Reported duration is less than one week; Fitzpatrick phototype III; located on the leg; an image taken at an angle; self-categorized by the patient as a rash: 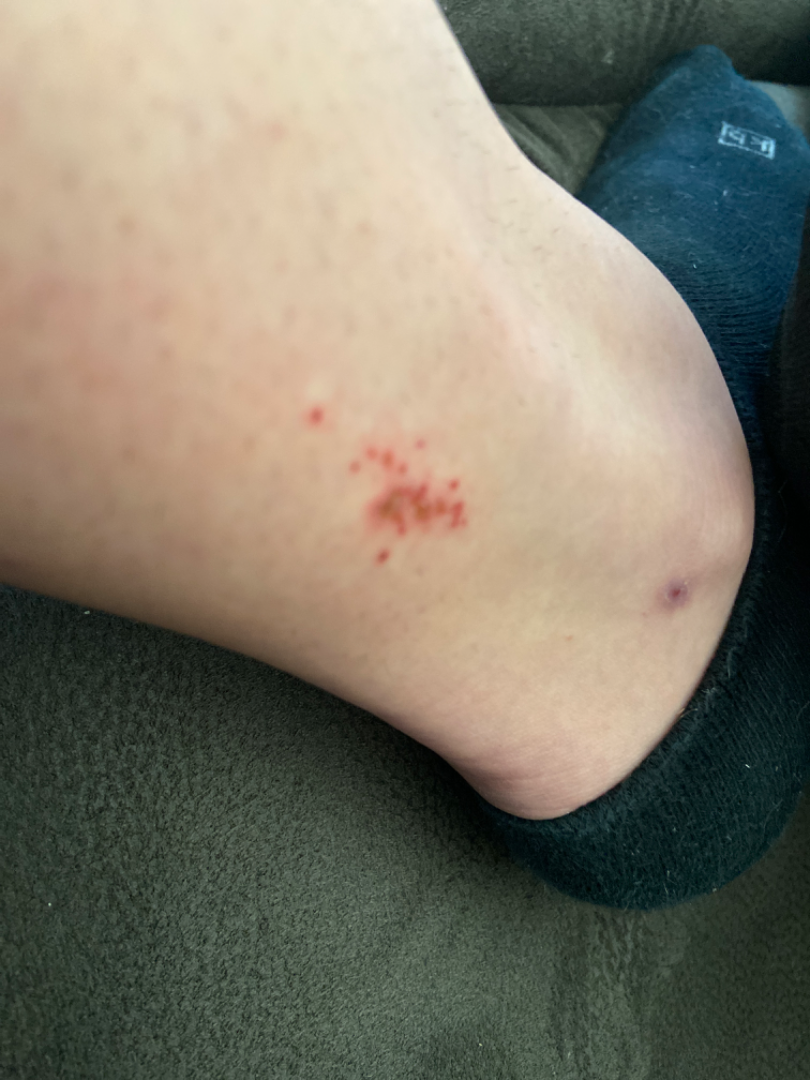| feature | finding |
|---|---|
| assessment | could not be assessed |